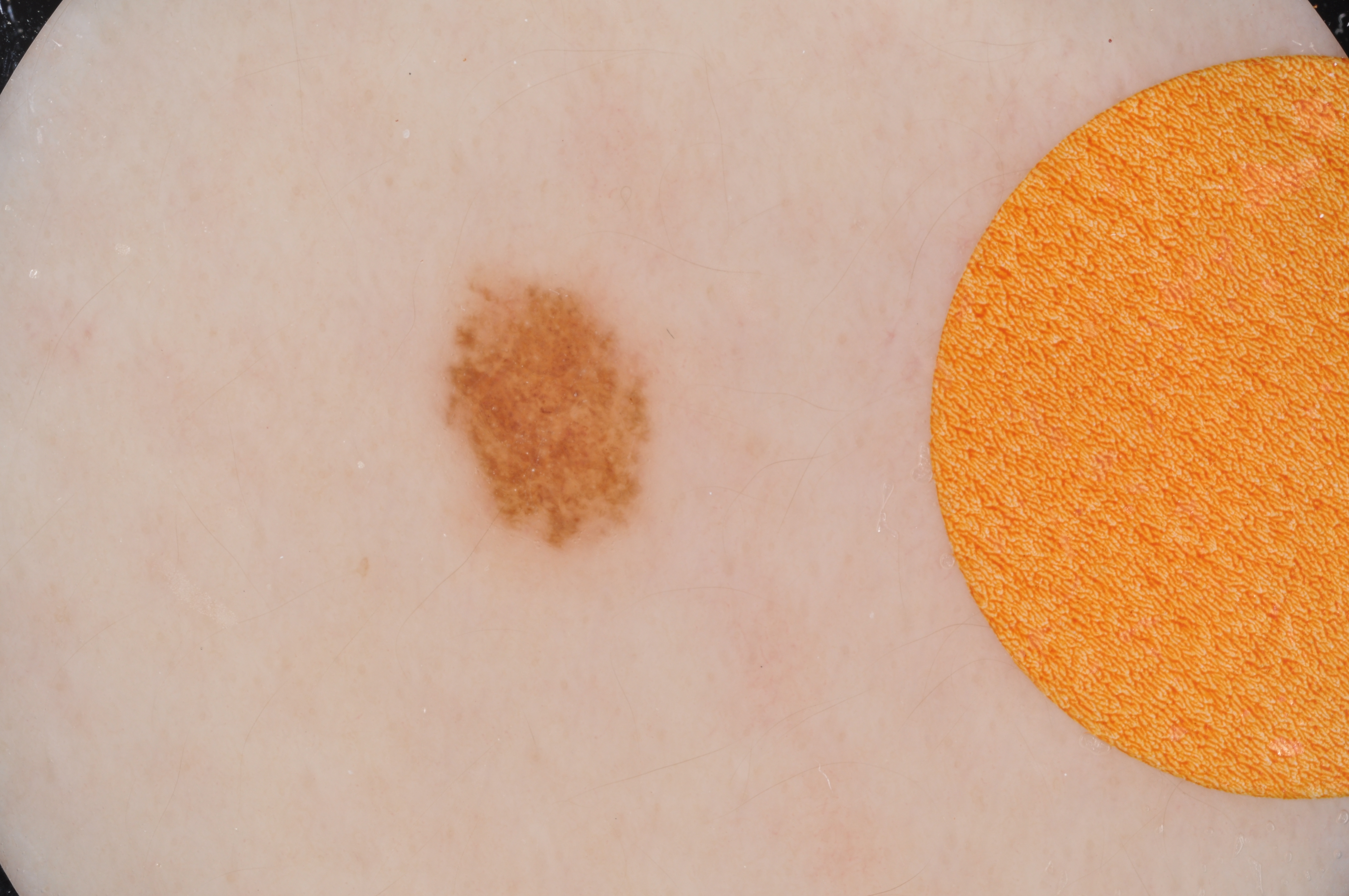Findings: The patient is a female roughly 15 years of age. A dermoscopic close-up of a skin lesion. The lesion occupies roughly 4% of the field. In (x1, y1, x2, y2) order, the lesion is bounded by 435/266/658/558. Dermoscopic examination shows no milia-like cysts, globules, pigment network, streaks, or negative network. Assessment: Diagnosed as a melanocytic nevus.